A dermoscopic close-up of a skin lesion.
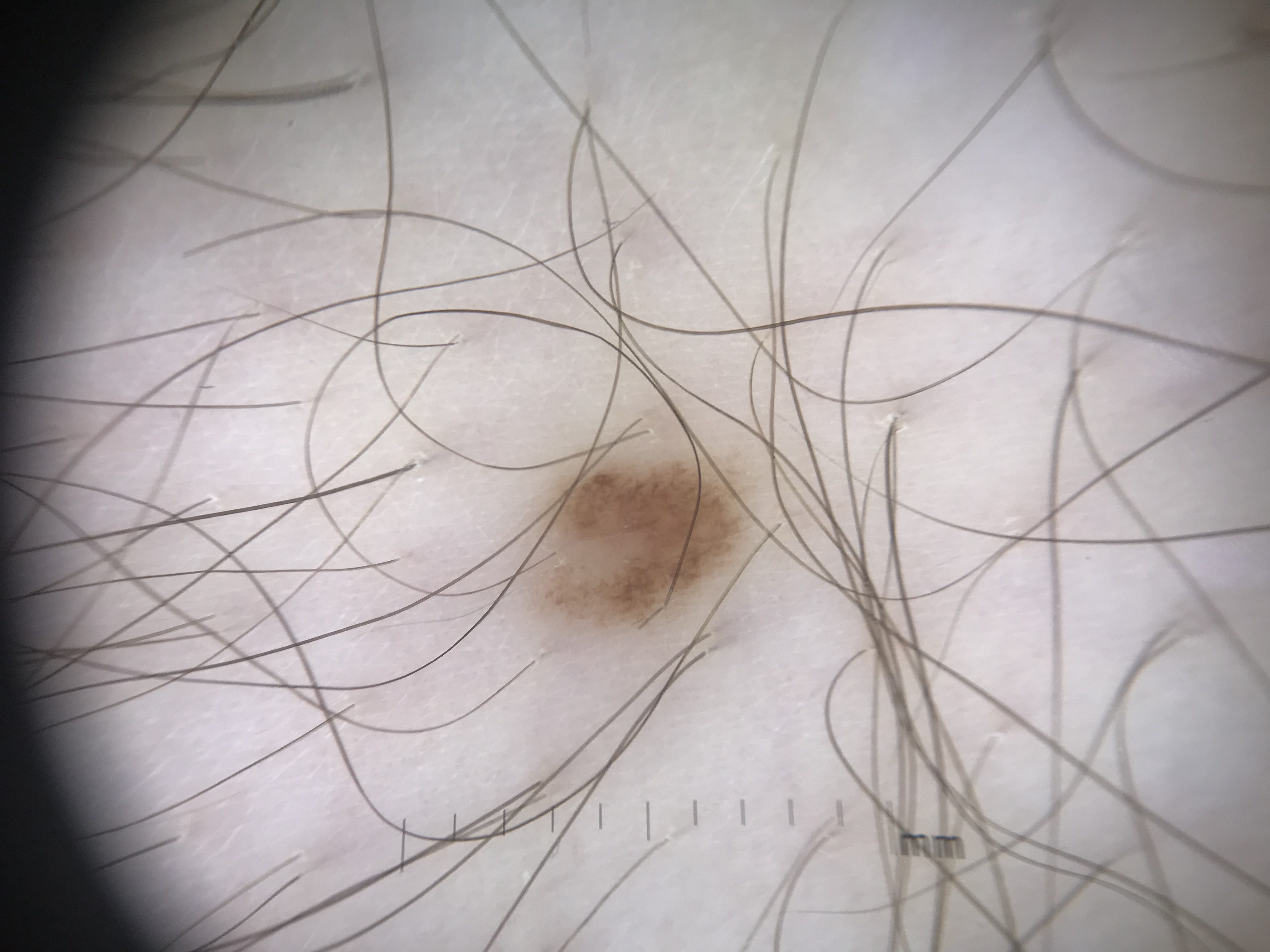Case:
* assessment · dysplastic junctional nevus (expert consensus)